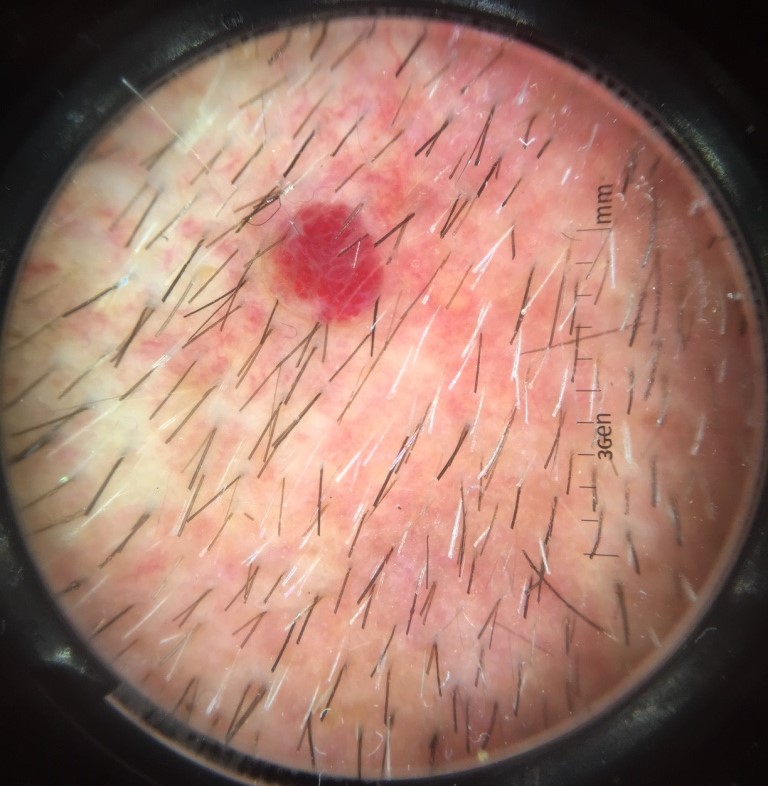Dermoscopy of a skin lesion. Diagnosed as a benign, vascular lesion — a hemangioma.